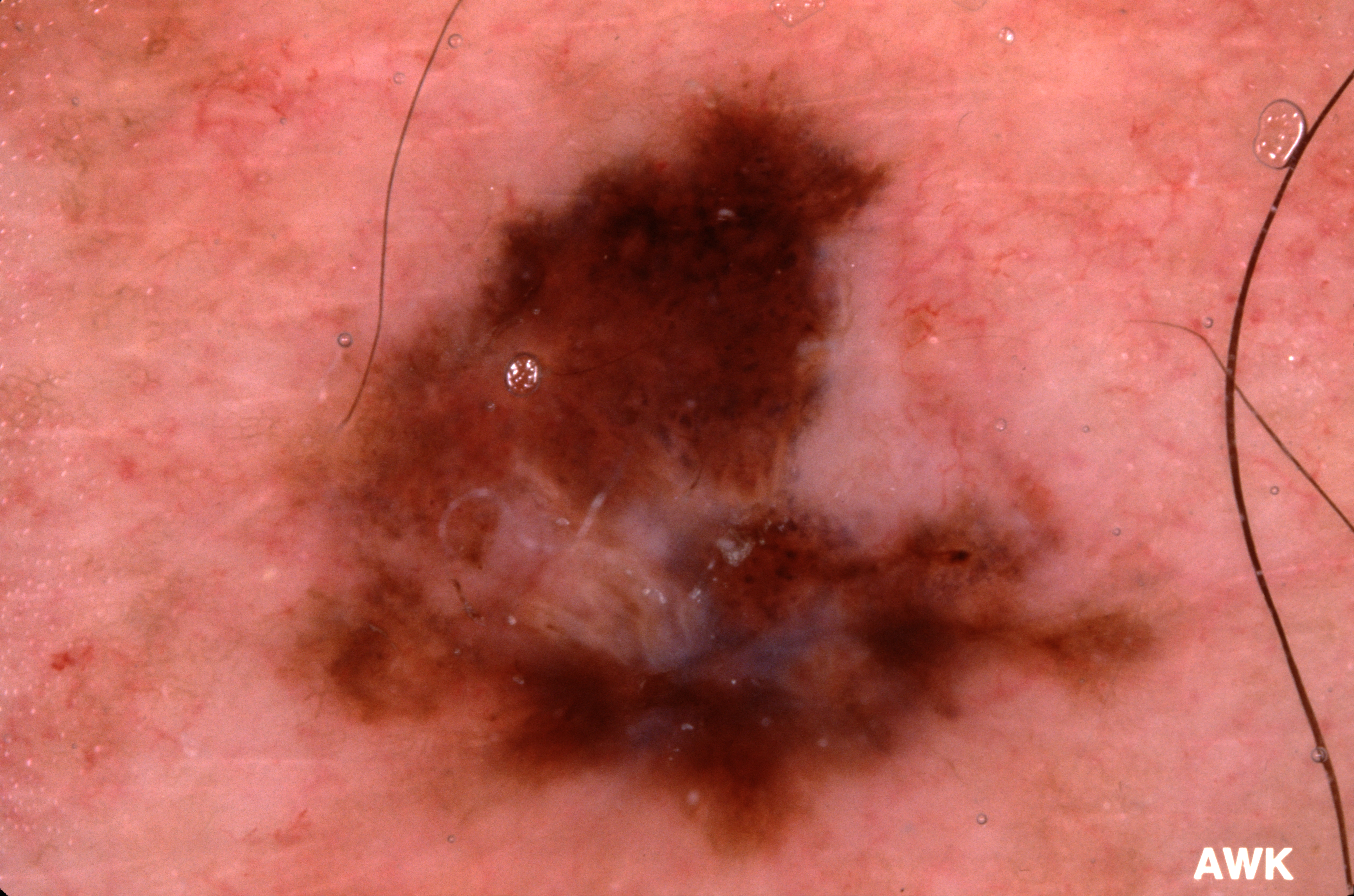A male subject, aged 73 to 77.
Dermoscopy of a skin lesion.
In (x1, y1, x2, y2) order, the lesion spans 185 50 1233 883.
Dermoscopically, the lesion shows pigment network.
Biopsy-confirmed as a melanoma, a skin cancer.